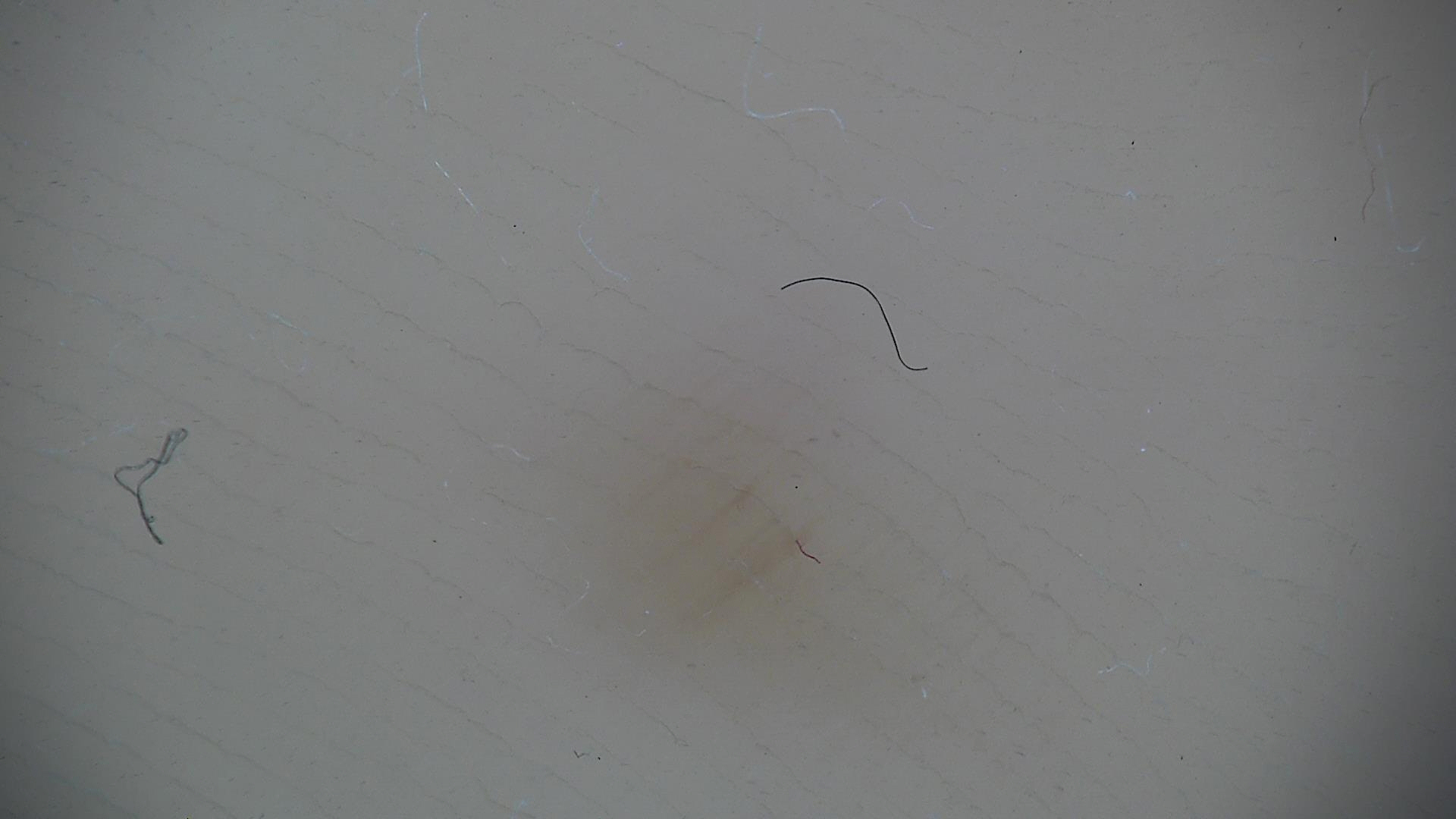A dermoscopic close-up of a skin lesion.
Classified as a benign lesion — an acral dysplastic junctional nevus.